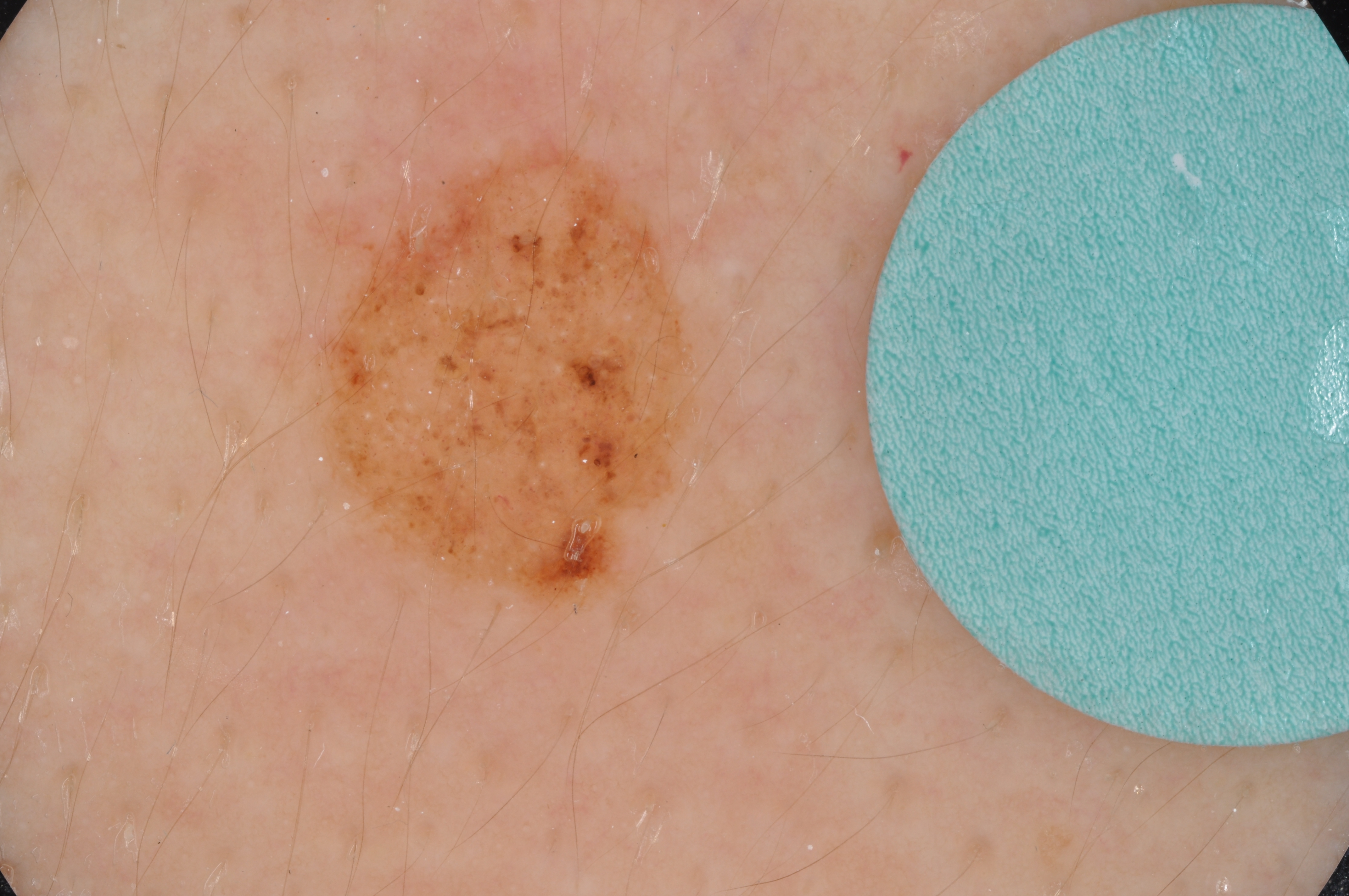Dermoscopy of a skin lesion.
A male patient, aged around 15.
A moderately sized lesion.
On dermoscopy, the lesion shows globules and milia-like cysts; no streaks, pigment network, or negative network.
Lesion location: box(321, 145, 712, 609).
Expert review diagnosed this as a melanocytic nevus.